The photograph was taken at an angle; the palm, top or side of the foot, sole of the foot, back of the hand and arm are involved; self-categorized by the patient as a rash; the patient notes itching, burning and pain; the lesion is described as raised or bumpy; the patient notes the condition has been present for more than one year; the patient is a female aged 18–29 — 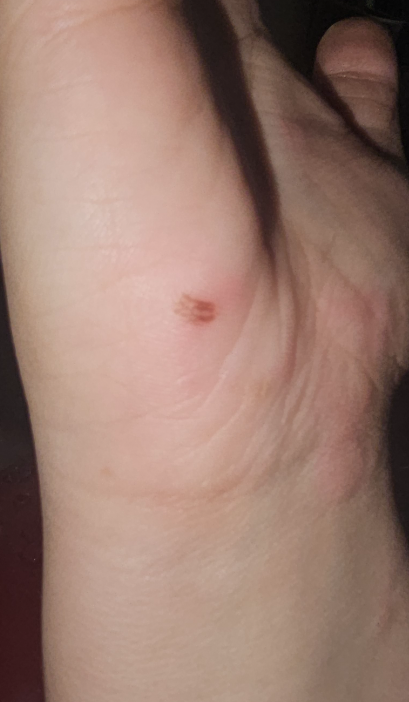On dermatologist assessment of the image, Drug Rash (weight 0.33); Urticaria (weight 0.33); Erythema multiforme (weight 0.33).